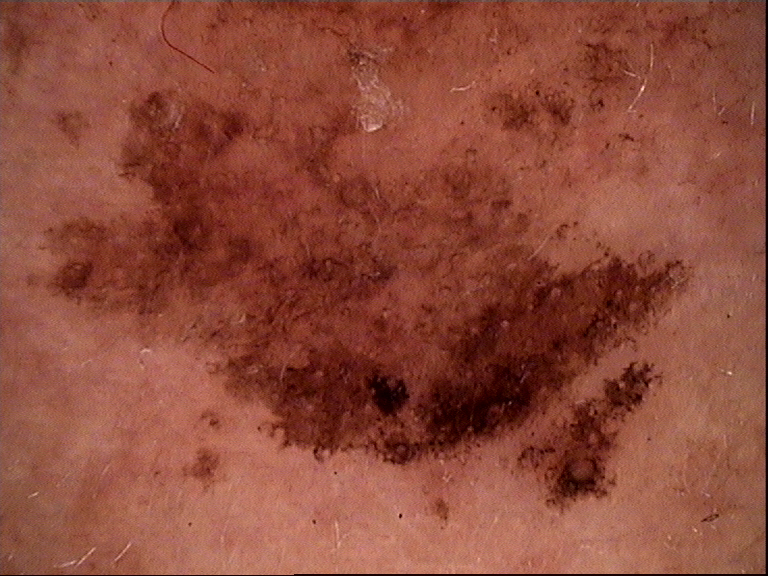diagnostic label: solar lentigo (expert consensus).